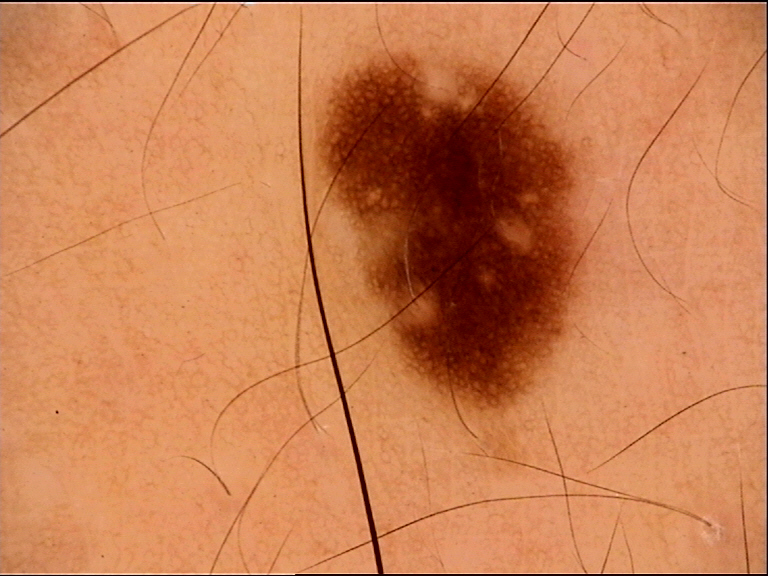Dermoscopy of a skin lesion.
The architecture is that of a banal lesion.
Classified as a junctional nevus.